The contributor is 40–49, female; located on the arm; this image was taken at an angle — 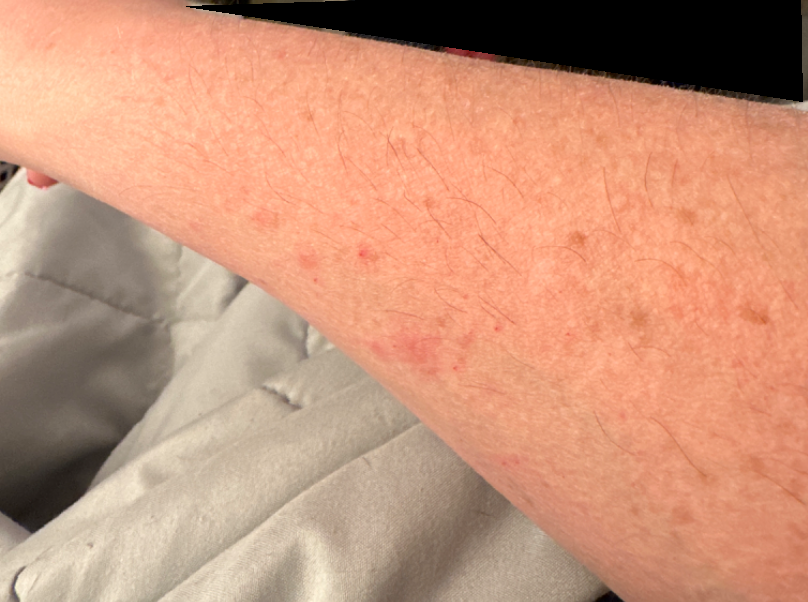Notes:
– assessment: Insect Bite, Eczema and Allergic Contact Dermatitis were considered with similar weight